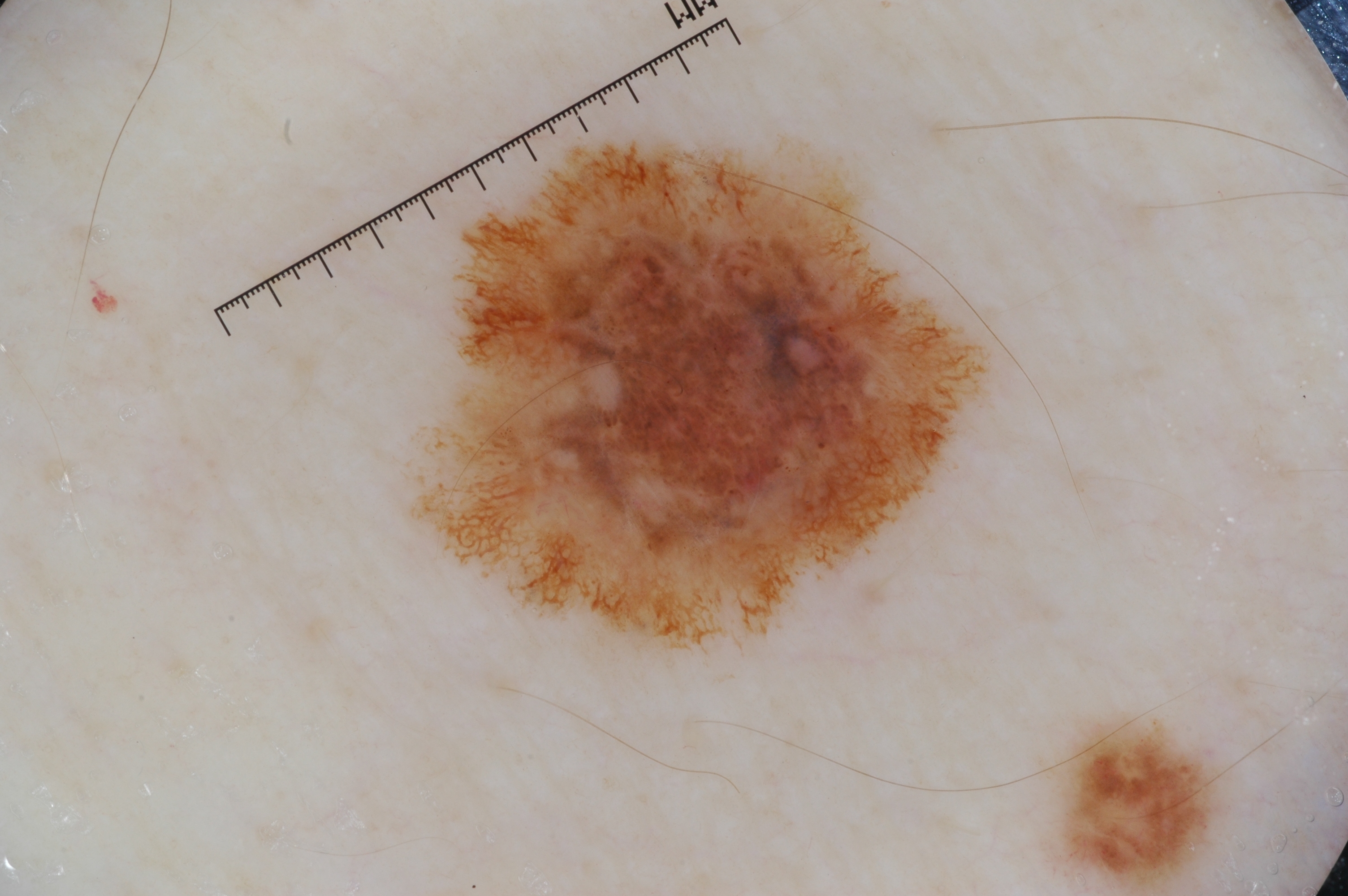– subject · male, aged 48-52
– image type · dermoscopy
– lesion location · [422,140,990,651]
– dermoscopic pattern · negative network and pigment network; absent: streaks and milia-like cysts
– size · ~17% of the field
– assessment · a melanoma, a malignant lesion